The referring clinician suspected basal cell carcinoma; the patient says their skin reddens with sun exposure; a male subject 81 years of age: 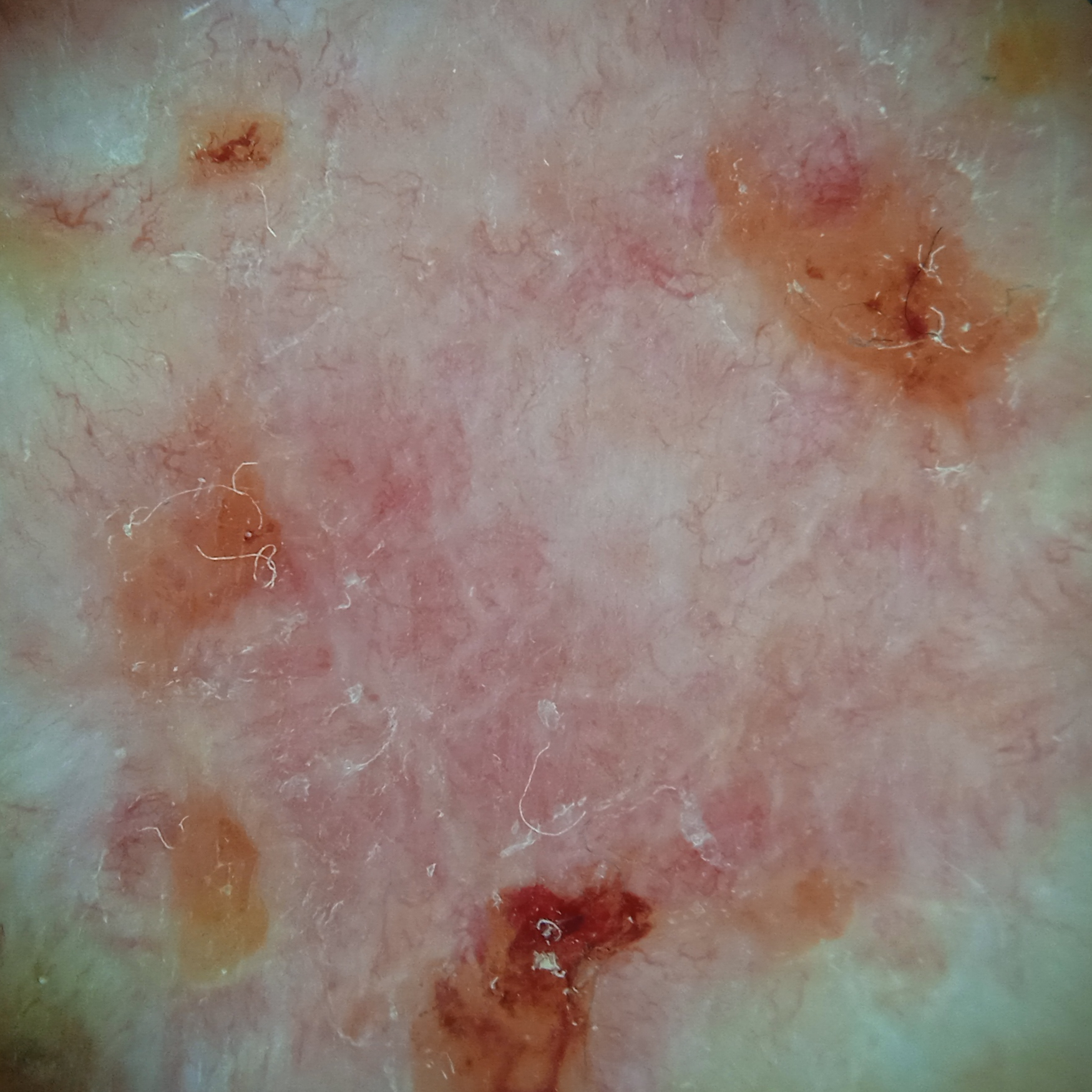The lesion is located on the back.
Confirmed on histopathology as a basal cell carcinoma, following excision, with a measured thickness of 3 mm.